A male subject roughly 50 years of age · a dermoscopic photograph of a skin lesion · Fitzpatrick phototype II.
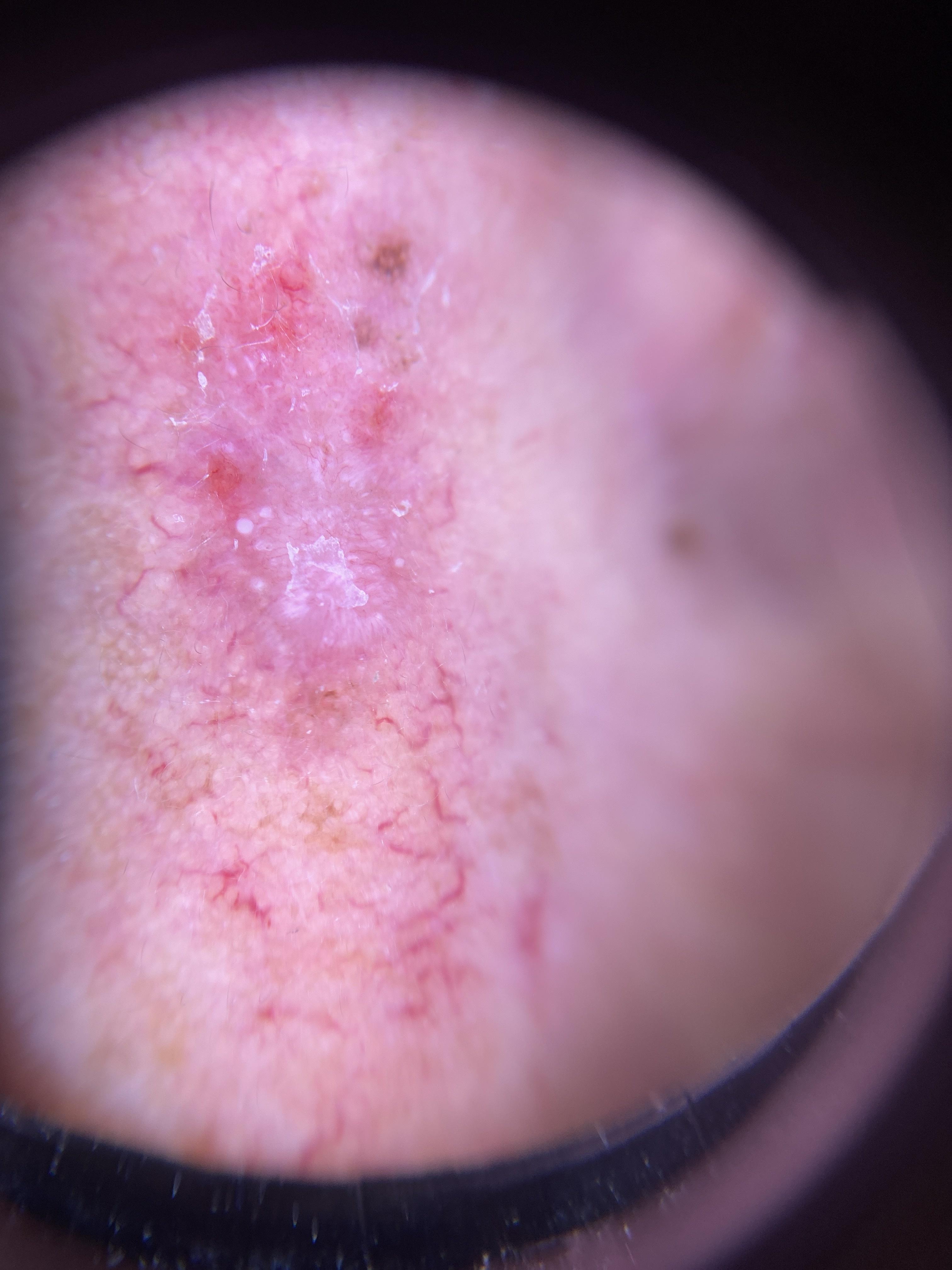{
  "lesion_location": {
    "region": "the head or neck"
  },
  "diagnosis": {
    "name": "Basal cell carcinoma",
    "malignancy": "malignant",
    "confirmation": "histopathology",
    "lineage": "adnexal"
  }
}